A male subject in their late 50s. The chart records pesticide exposure, prior skin cancer (patient or family), prior malignancy (patient or family), and no tobacco use. Recorded as skin type I. A clinical photo of a skin lesion taken with a smartphone.
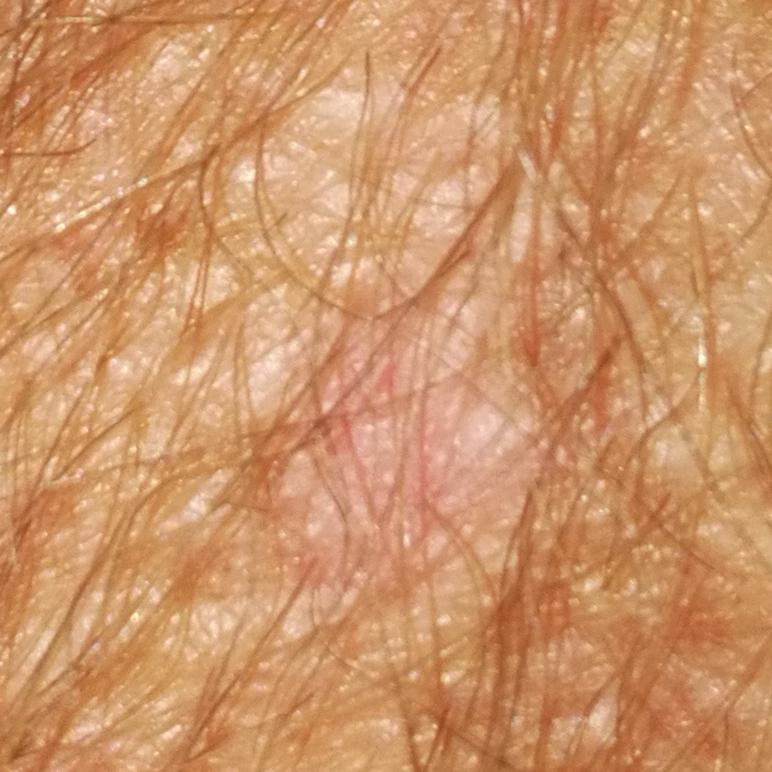The lesion involves an arm. The lesion is roughly 10 by 7 mm. The patient describes that the lesion does not itch and has not changed. Consistent with an actinic keratosis.